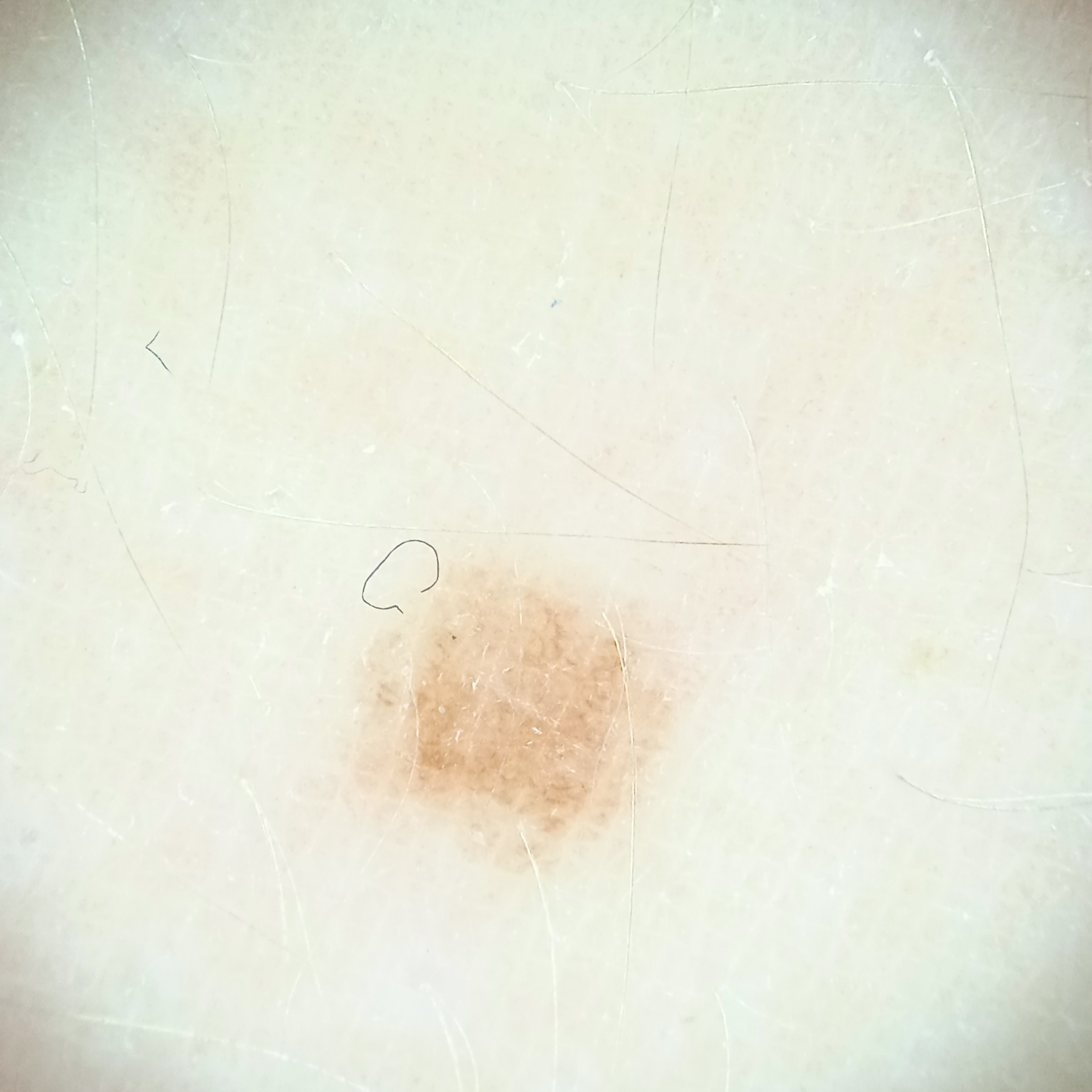{"diagnosis": {"name": "melanocytic nevus", "malignancy": "benign"}}